An image taken at a distance, the patient reports bothersome appearance, the patient reports the condition has been present for more than five years, texture is reported as raised or bumpy and rough or flaky, the patient is a female aged 40–49, the patient considered this acne: 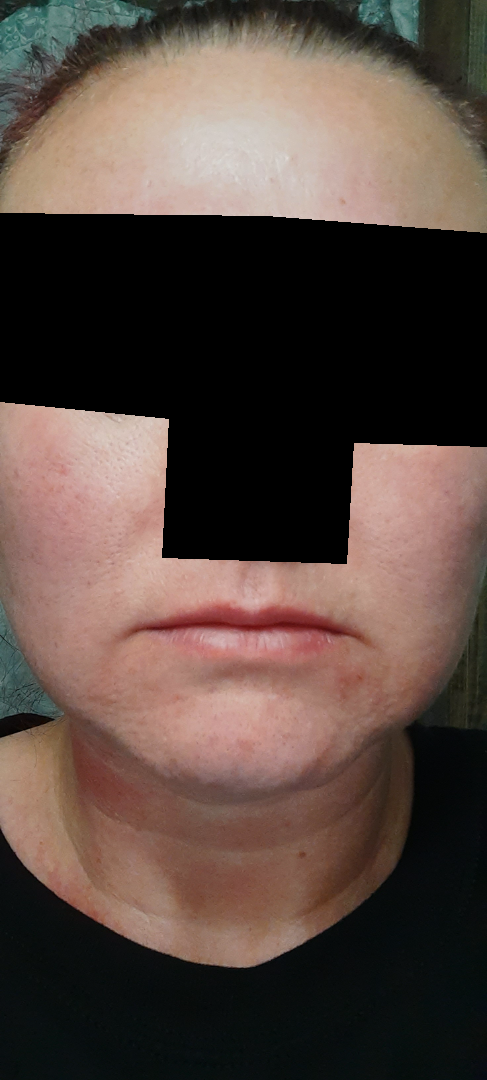Q: What is the dermatologist's impression?
A: three independent reviewers: favoring Perioral Dermatitis; with consideration of Irritant Contact Dermatitis; less likely is Perleche; less probable is Seborrheic Dermatitis; a remote consideration is Acne